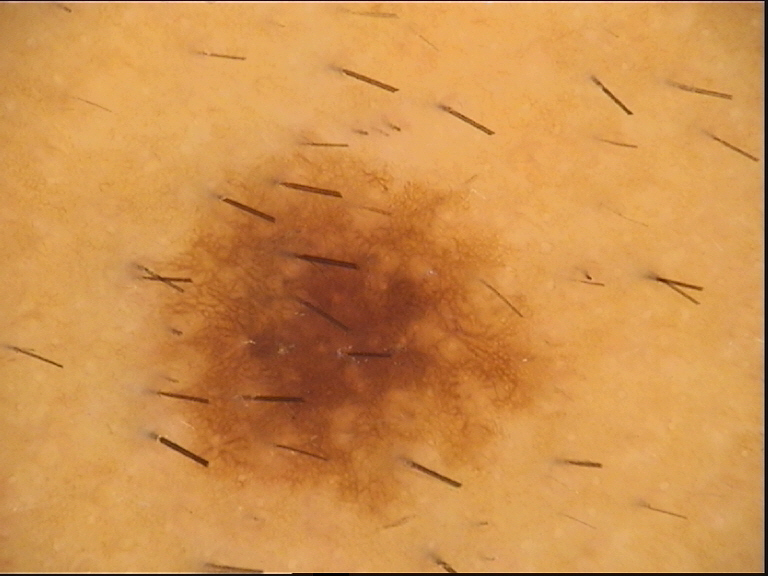{
  "diagnosis": {
    "name": "dysplastic junctional nevus",
    "code": "jd",
    "malignancy": "benign",
    "super_class": "melanocytic",
    "confirmation": "expert consensus"
  }
}